A close-up photograph: 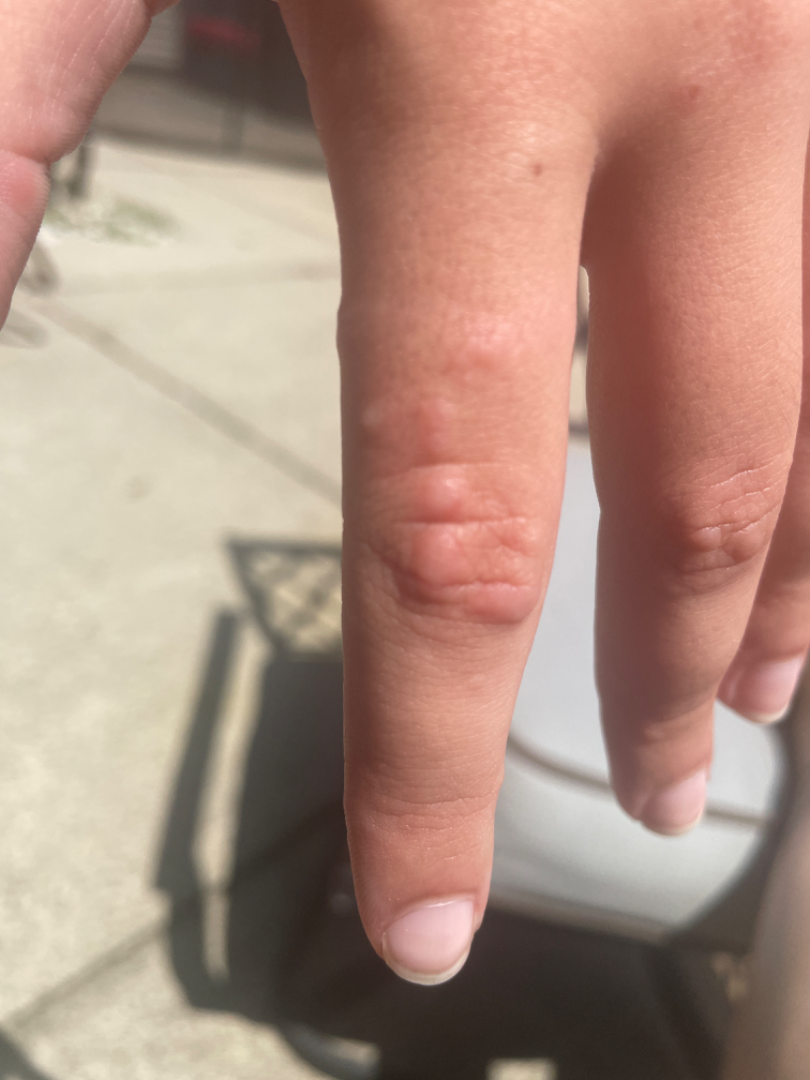Findings: On teledermatology review: Rheumatoid nodule (considered); Granuloma annulare (considered).